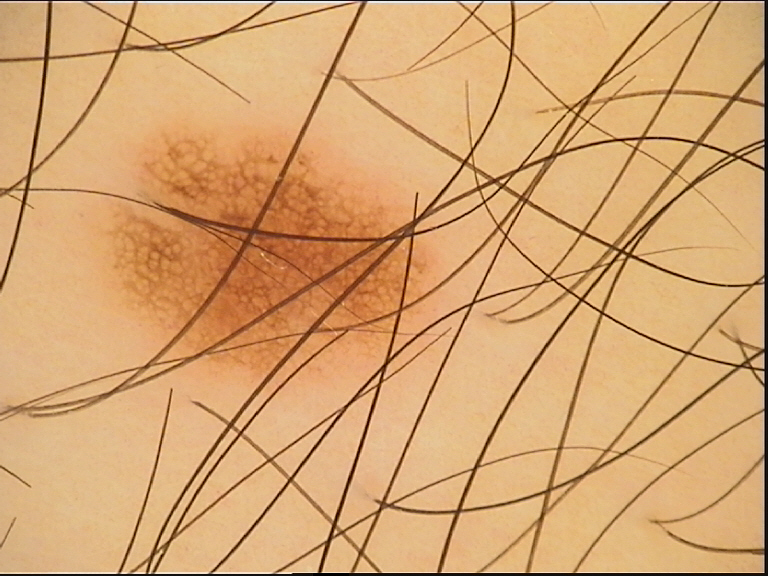Consistent with a banal lesion — a junctional nevus.